Dermoscopy of a skin lesion.
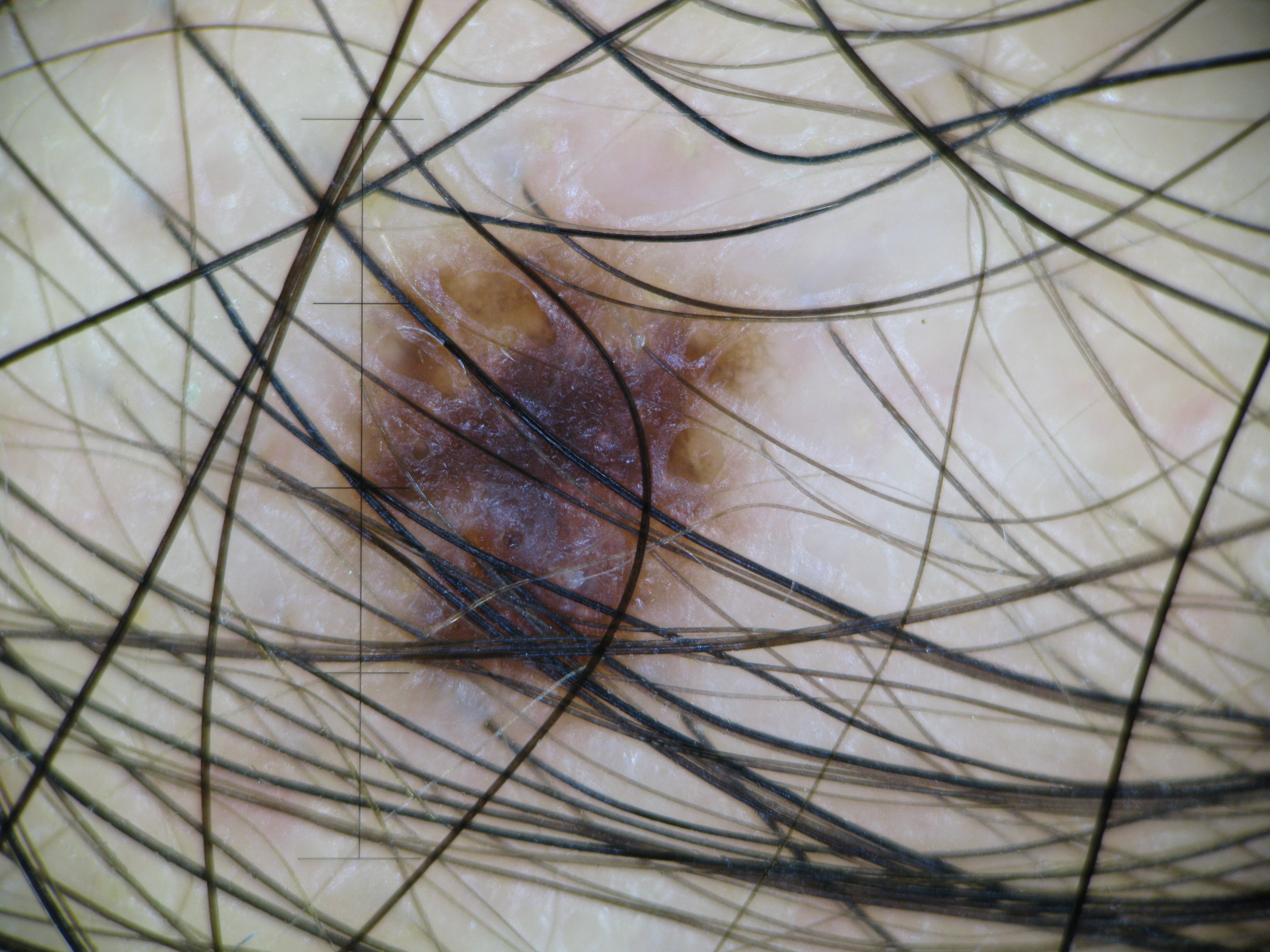Diagnosed as a dysplastic junctional nevus.